A dermoscopic photograph of a skin lesion:
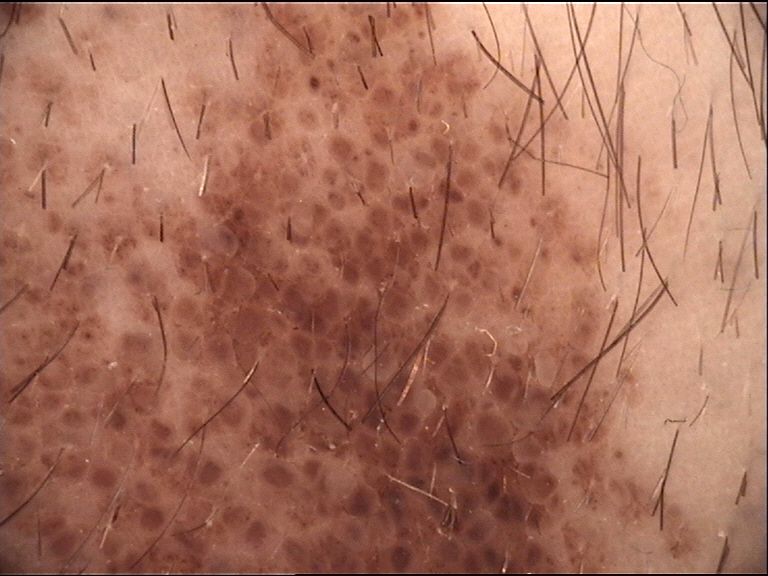classification: banal | label: congenital compound nevus (expert consensus).